The subject is 30–39, male. Located on the leg. The photograph was taken at a distance.
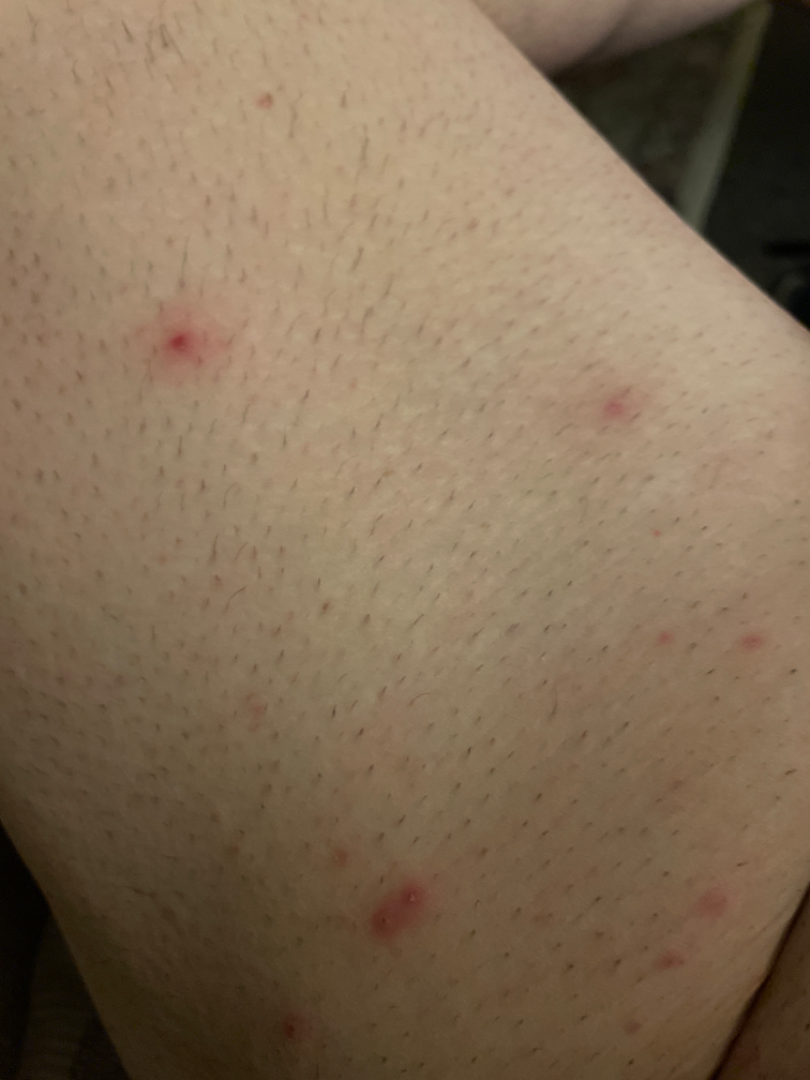{
  "differential": {
    "leading": [
      "Folliculitis"
    ]
  }
}